A dermoscopic close-up of a skin lesion: 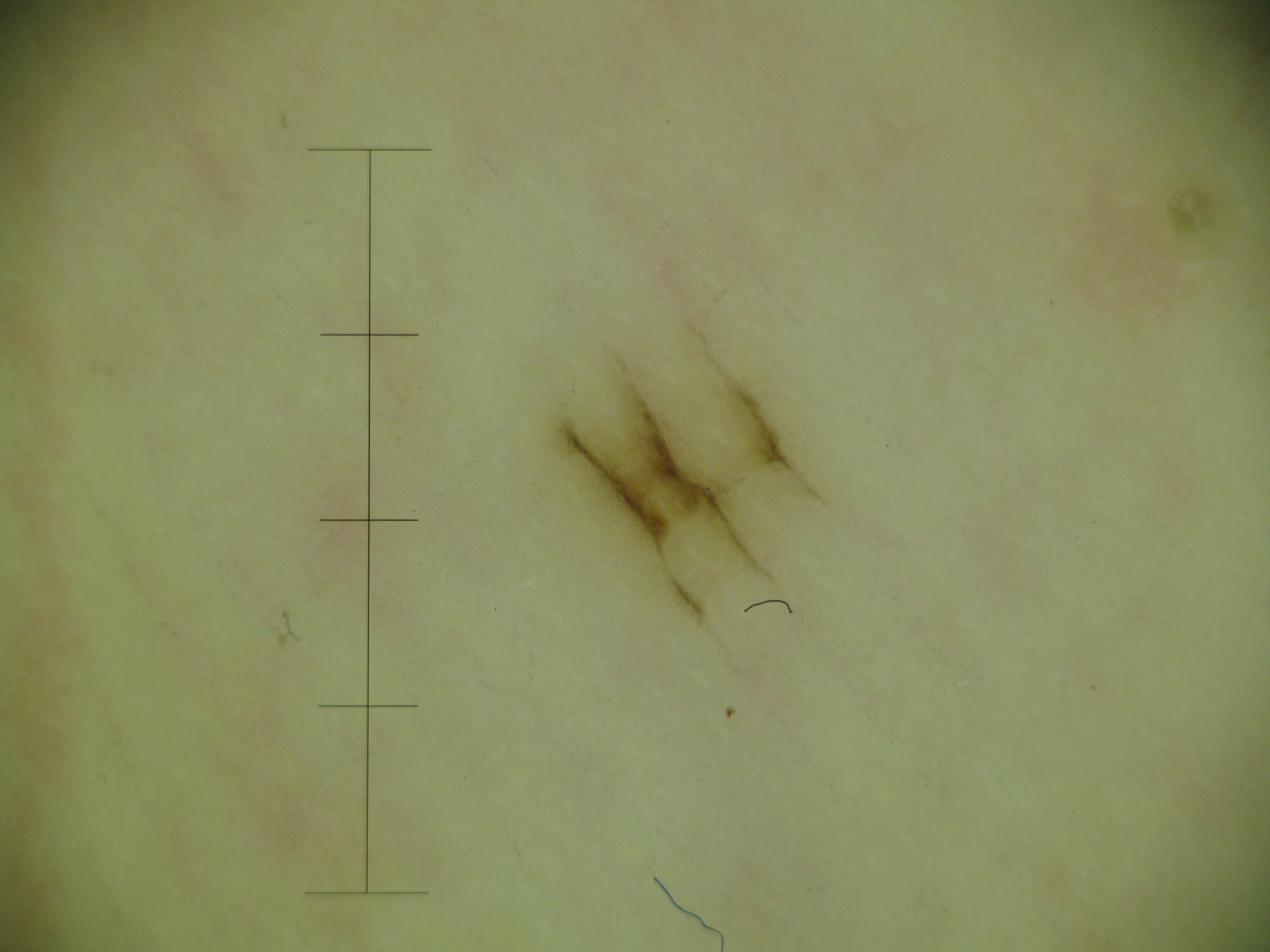assessment = acral junctional nevus (expert consensus).